A dermatoscopic image of a skin lesion · a female patient, approximately 30 years of age: 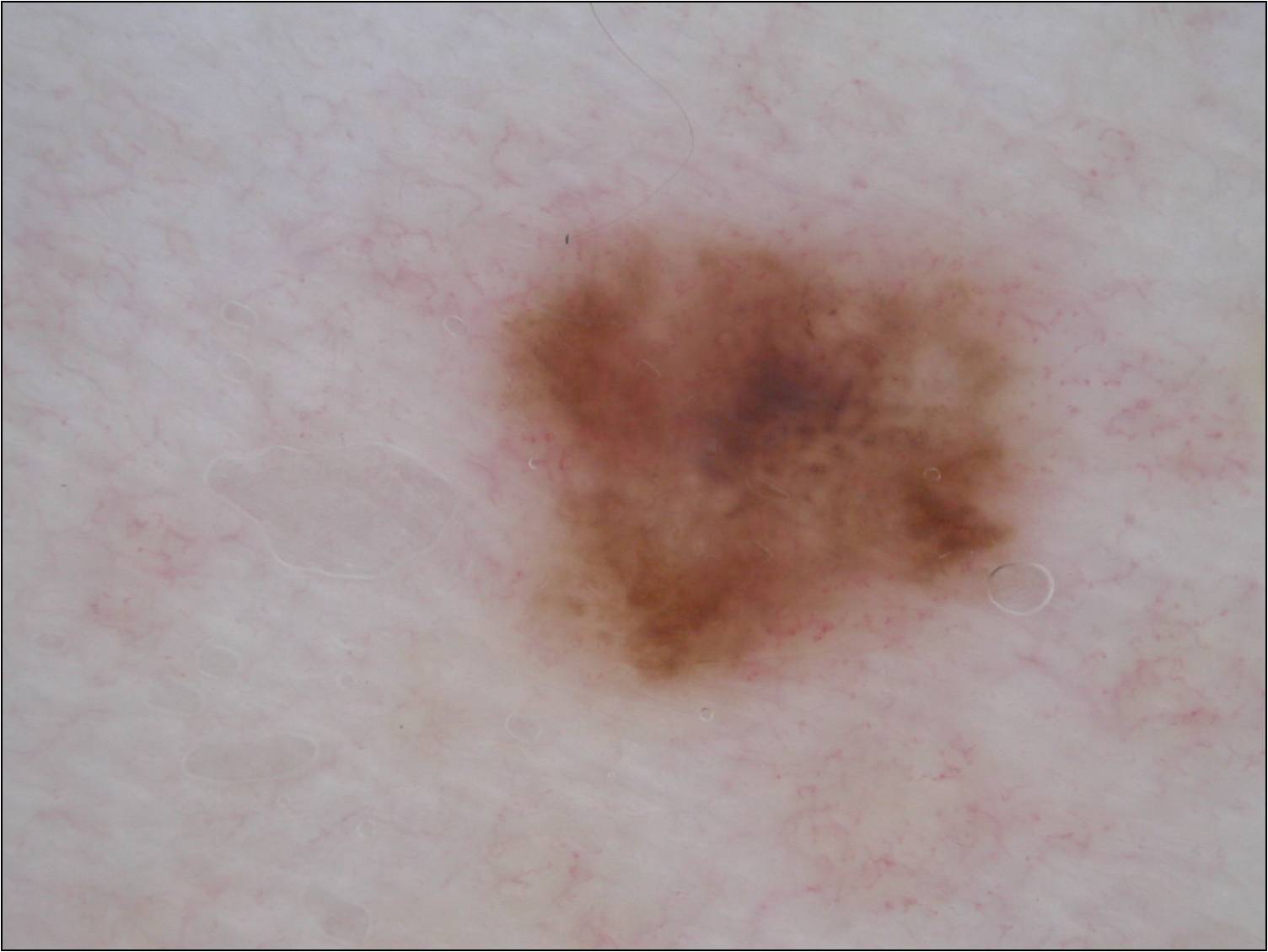The lesion occupies roughly 17% of the field. Dermoscopic review identifies globules, with no pigment network, streaks, milia-like cysts, or negative network. The lesion is located at <bbox>487, 224, 1042, 698</bbox>. Consistent with a melanocytic nevus, a benign skin lesion.